The patient says their skin reddens with sun exposure. A female subject 54 years old: 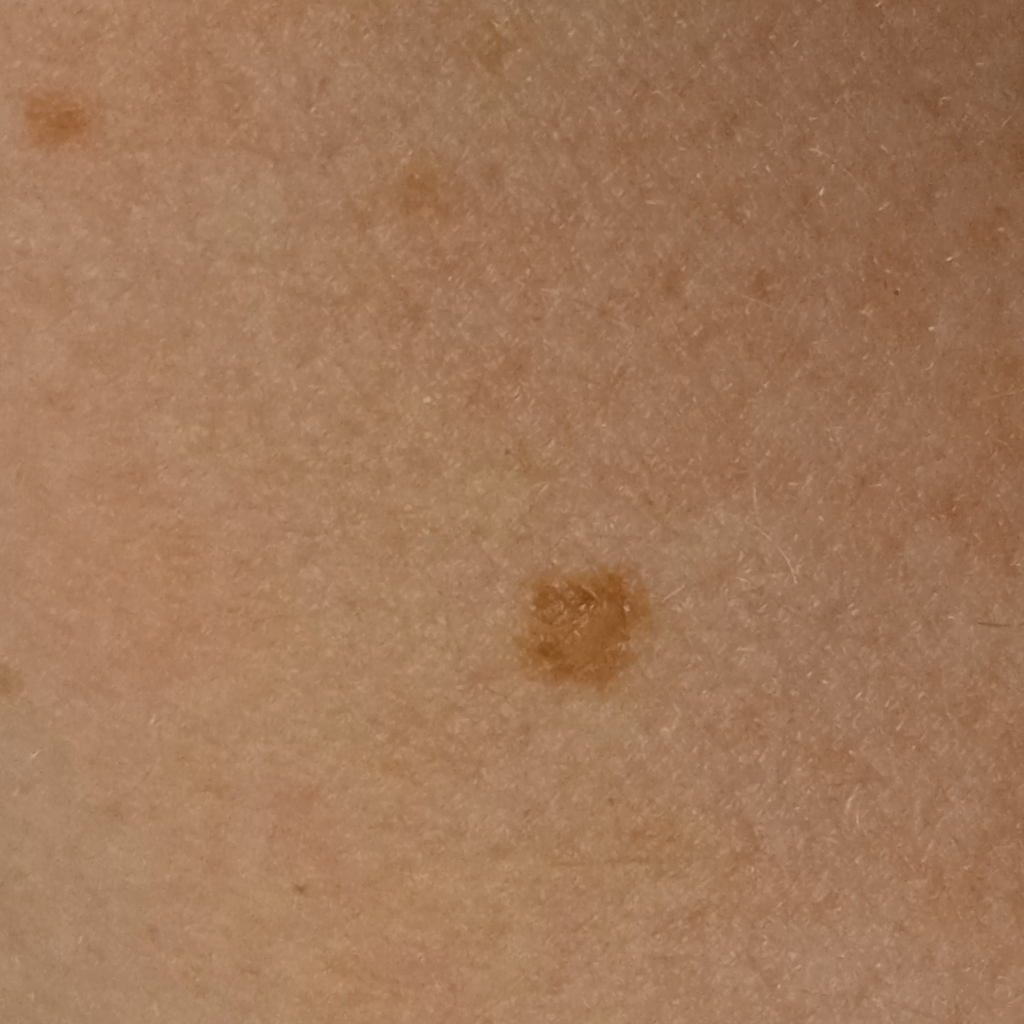Clinical context: The lesion measures approximately 4.7 mm. Conclusion: The diagnostic impression was an atypical (dysplastic) nevus.